Texture is reported as raised or bumpy and rough or flaky. Reported lesion symptoms include enlargement, itching, darkening, bothersome appearance and burning. The patient considered this a rash. The photo was captured at a distance. The condition has been present for less than one week. Male patient, age 40–49. The patient reported no systemic symptoms. Located on the back of the torso, front of the torso, leg and arm:
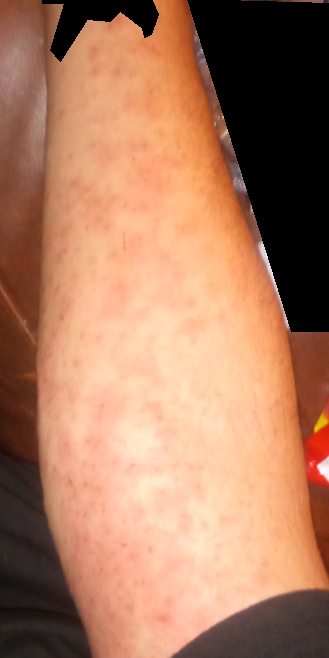The reviewer was unable to grade this case for skin condition.